Reported lesion symptoms include itching, enlargement and bothersome appearance. Close-up view. The contributor reports the condition has been present for one to three months. The affected area is the leg. Fitzpatrick skin type IV; human graders estimated MST 4 (US pool) or 1 (India pool). The contributor is a female aged 50–59 — 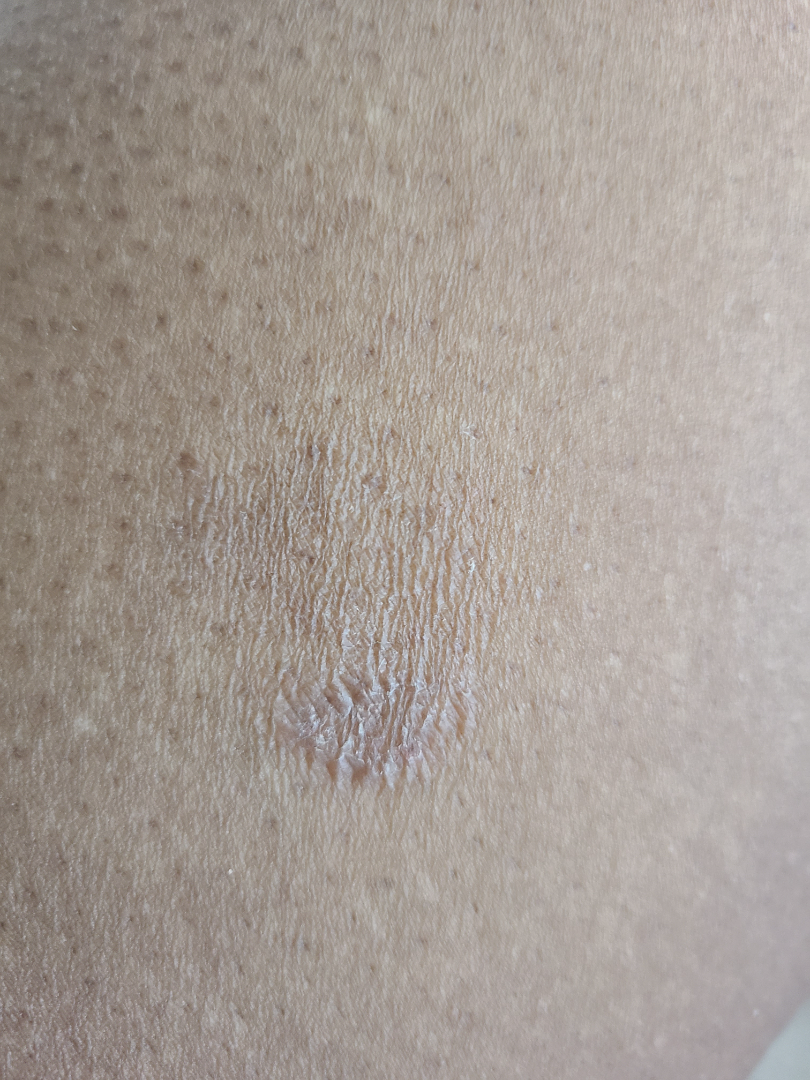| feature | finding |
|---|---|
| impression | a single dermatologist reviewed the case: the differential, in no particular order, includes Eczema, Pityriasis rosea and Psoriasis |